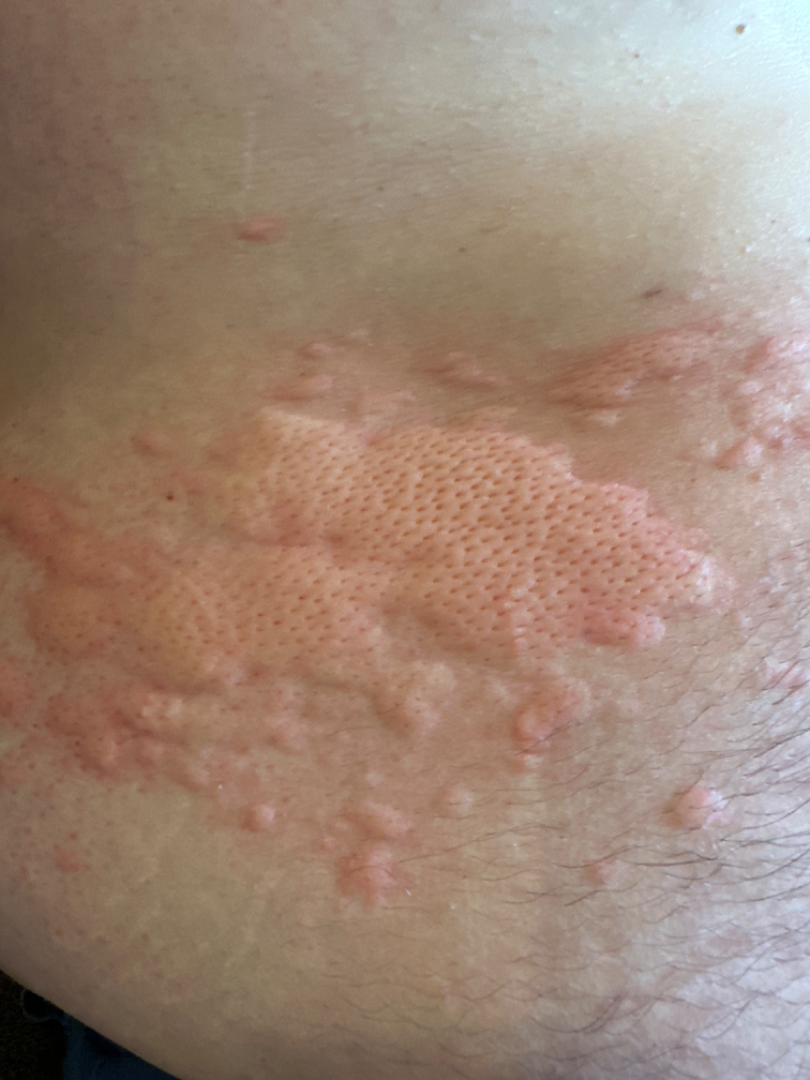The back of the torso and front of the torso are involved.
This is a close-up image.
Skin tone: FST III.
Present for about one day.
Consistent with Urticaria.